A dermoscopic photograph of a skin lesion.
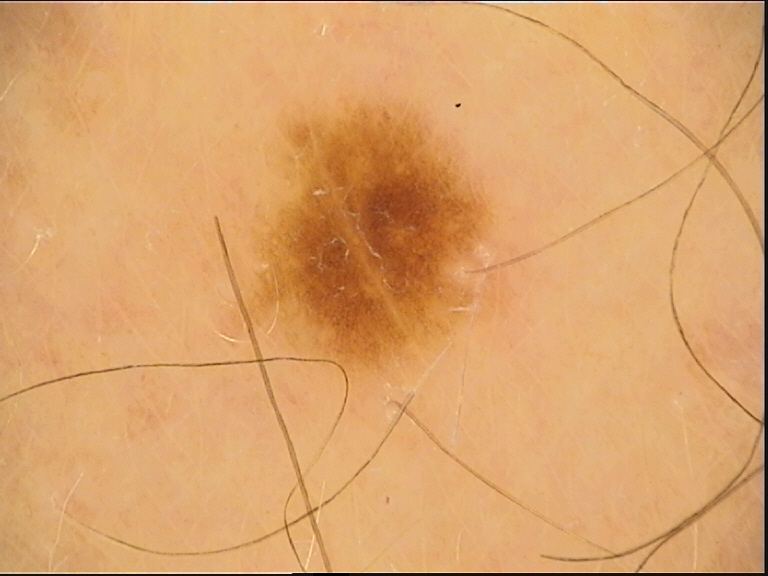class=dysplastic junctional nevus (expert consensus)